A dermoscopic photograph of a skin lesion: 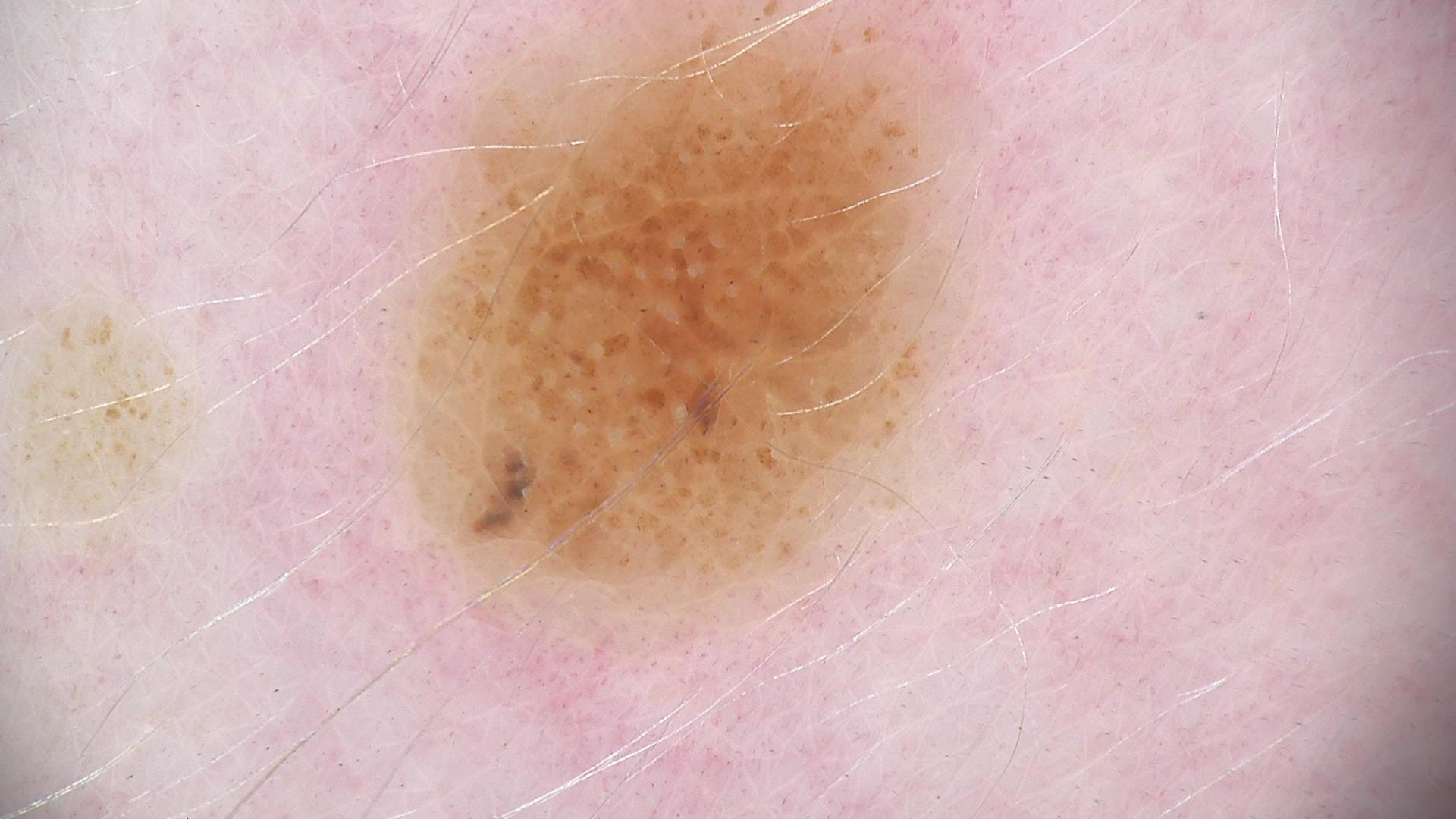Findings:
- subtype · banal
- diagnosis · compound nevus (expert consensus)